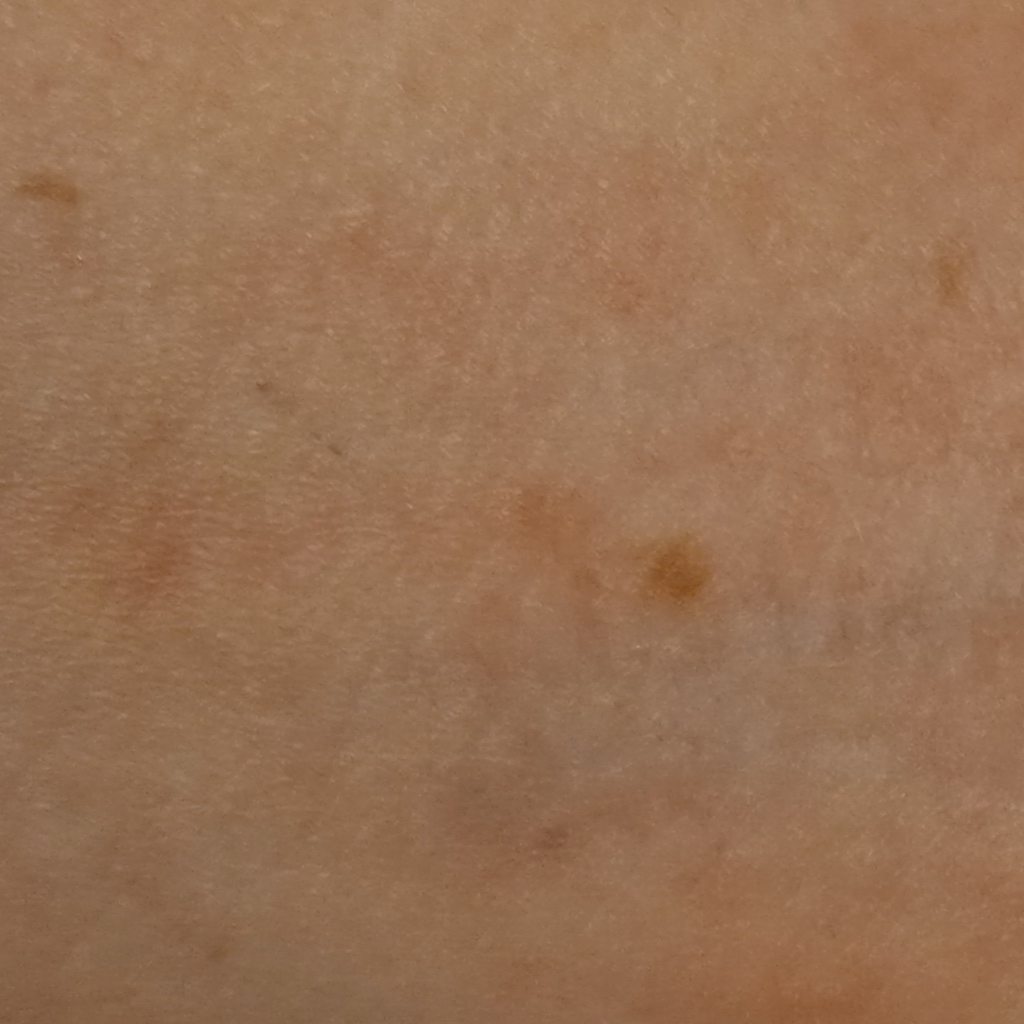Collected as part of a research study, without a referral diagnosis.
The patient describes having a moderate number of moles.
A clinical photograph showing a skin lesion.
The patient says their skin reddens with sun exposure.
The lesion is located on an arm.
Measuring roughly 6.5 mm.
The diagnostic impression was a melanocytic nevus.